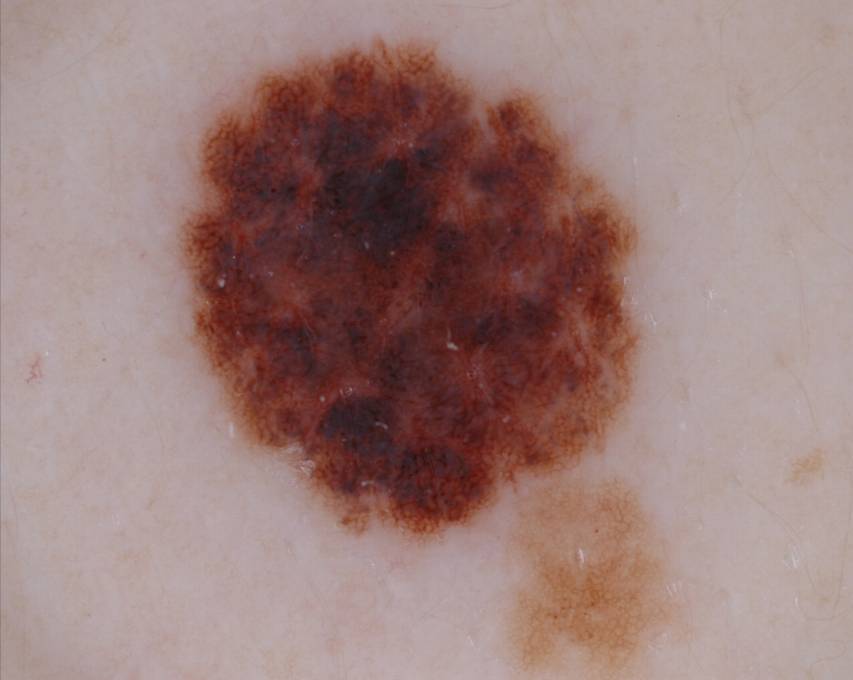| key | value |
|---|---|
| imaging | dermatoscopic image of a skin lesion |
| lesion bbox | bbox(182, 40, 634, 536) |
| dermoscopic findings | globules and pigment network |
| diagnosis | a melanocytic nevus, a benign lesion |